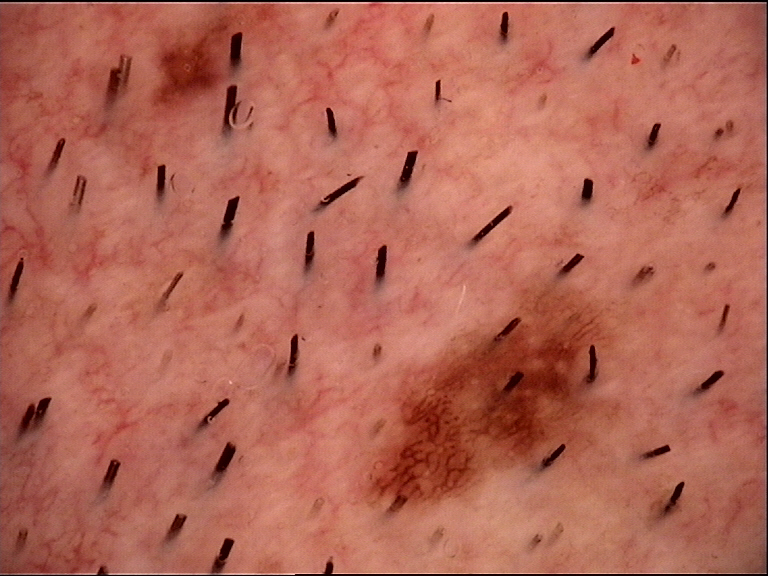Consistent with a dysplastic junctional nevus.